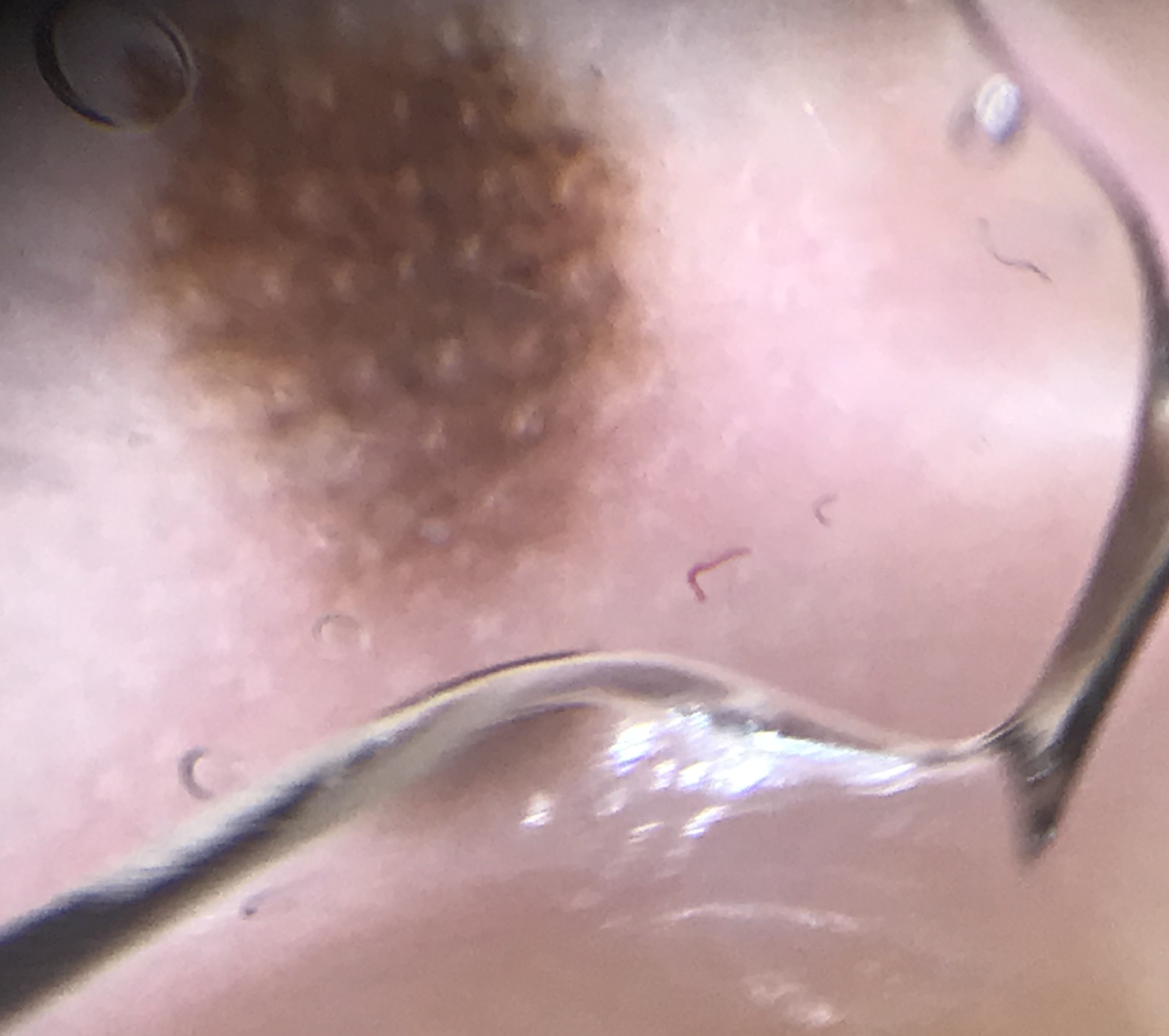image type=dermoscopy
category=banal
diagnostic label=acral junctional nevus (expert consensus)